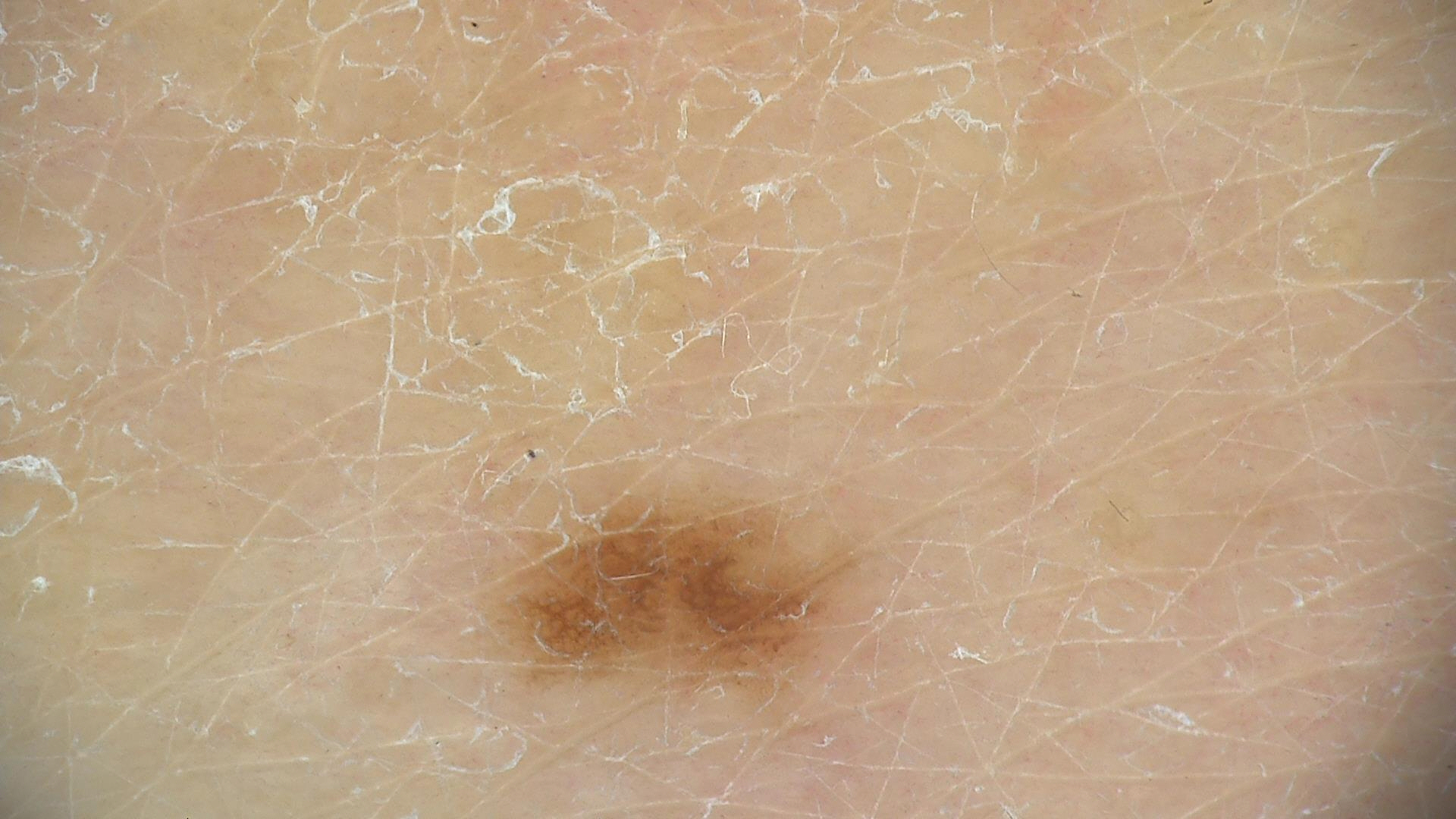Q: What was the diagnostic impression?
A: dysplastic junctional nevus (expert consensus)